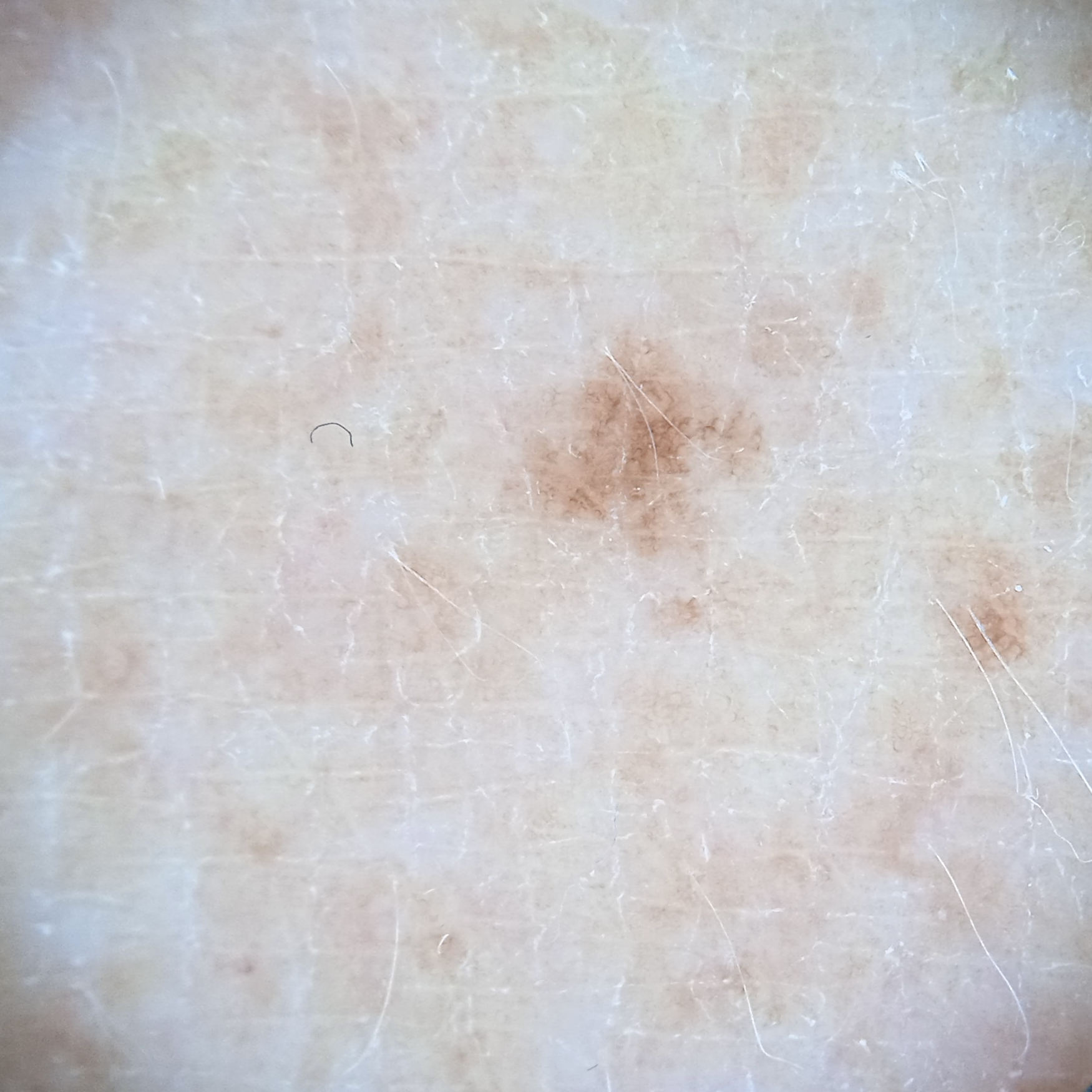{"sun_reaction": "skin tans without first burning", "referral": "research study (no referral diagnosis)", "mole_burden": "a moderate number of melanocytic nevi", "image": "dermatoscopic image", "patient": {"age": 54, "sex": "male"}, "lesion_location": "an arm", "lesion_size": {"diameter_mm": 2.6}, "diagnosis": {"name": "melanocytic nevus", "malignancy": "benign"}}